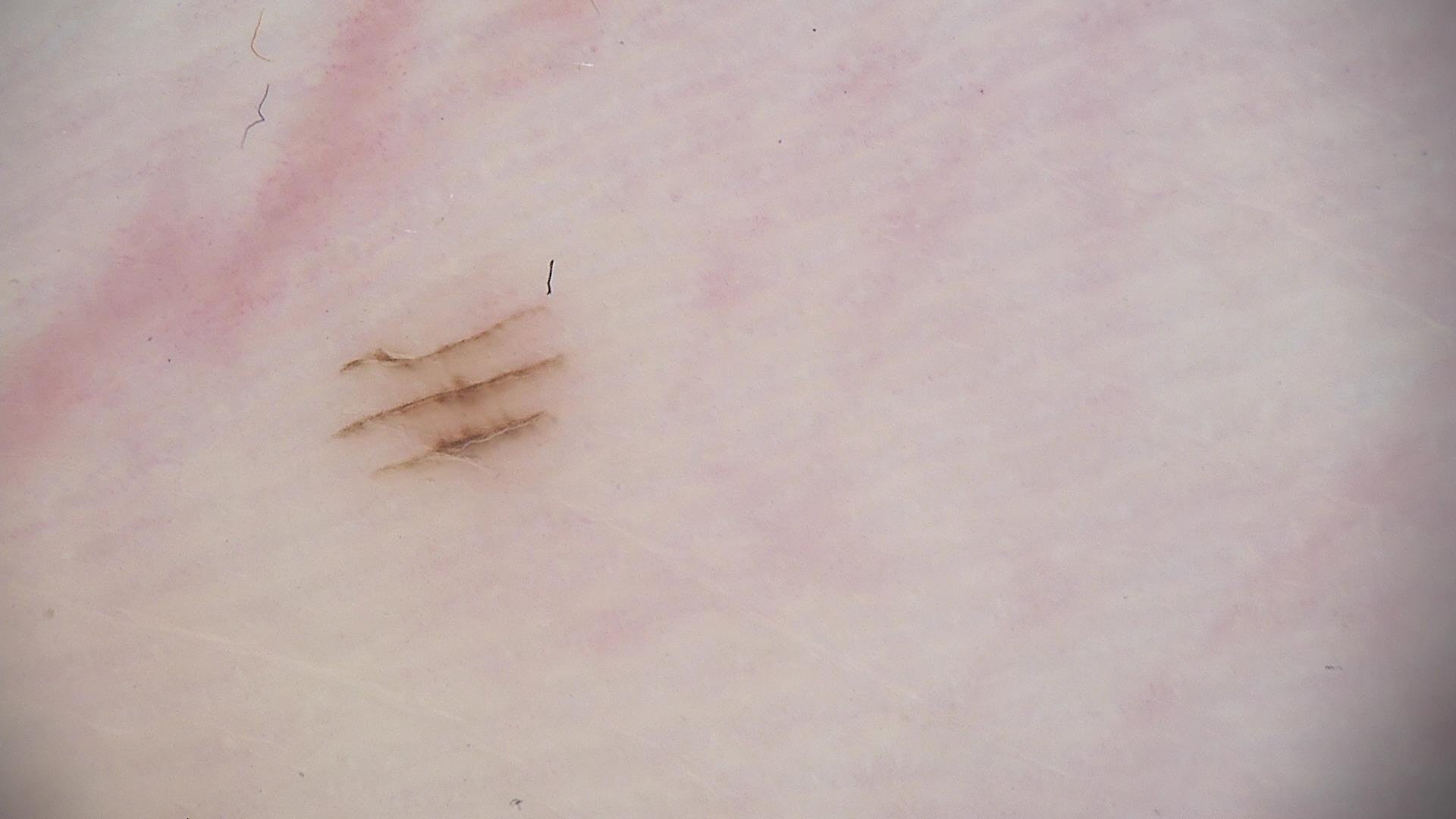Conclusion: Consistent with an acral dysplastic junctional nevus.